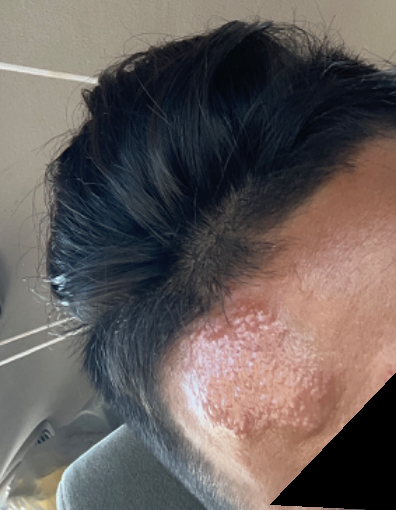| field | value |
|---|---|
| contributor | male |
| symptom duration | about one day |
| texture | fluid-filled and raised or bumpy |
| reported symptoms | none reported |
| photo taken | at a distance |
| self-categorized as | a rash |
| associated systemic symptoms | none reported |
| site | head or neck |
| clinical impression | the differential, in no particular order, includes Impetigo, Granuloma faciale, Herpes Simplex, Crohn disease of skin, Localised skin infection and Granulomatous disorder of the skin and subcutaneous tissue |